The patient says their skin reddens with sun exposure · dermoscopy of a skin lesion · acquired for a research image collection, with no referral diagnosis — 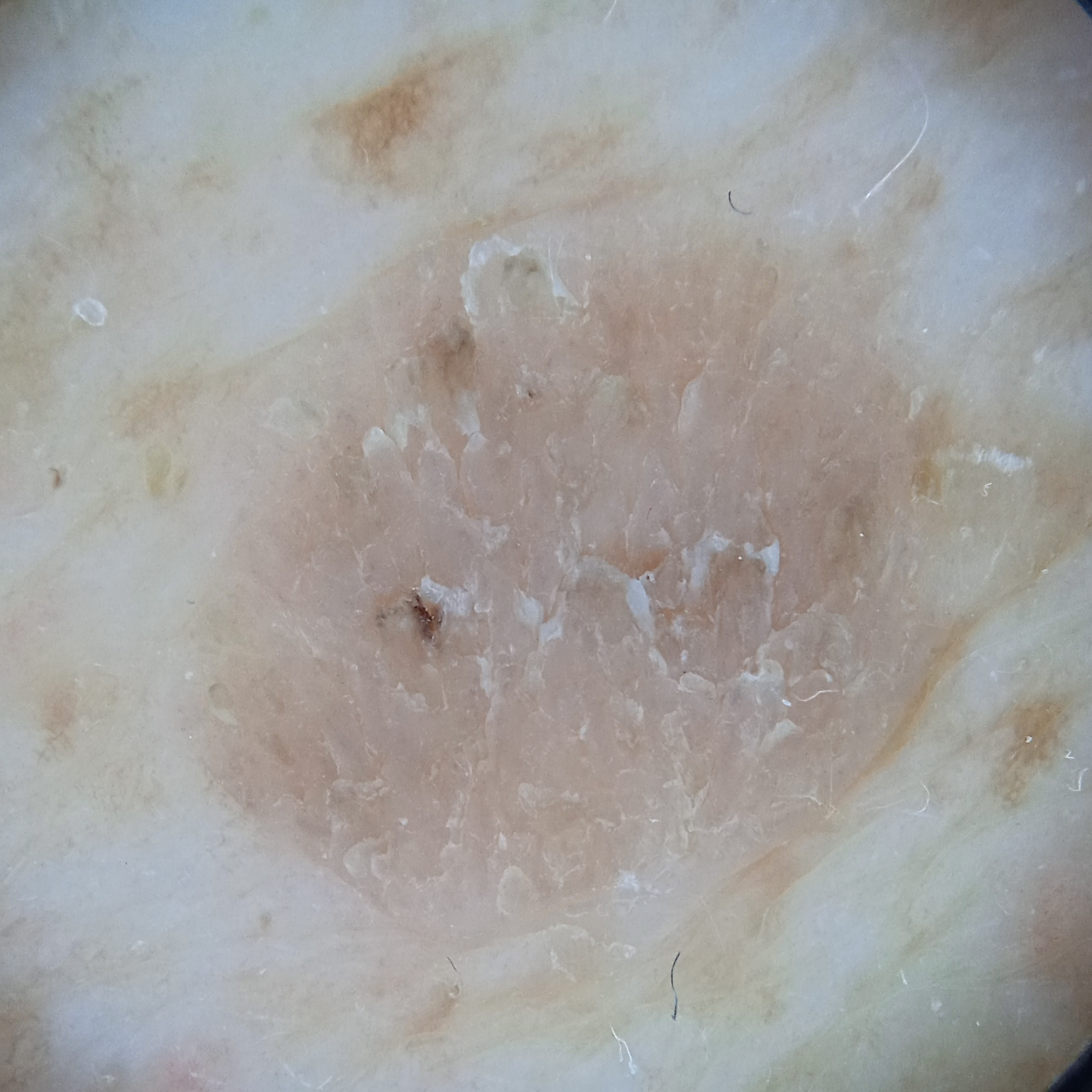The lesion is located on the back.
Measuring roughly 9.5 mm.
The lesion was assessed as a seborrheic keratosis.